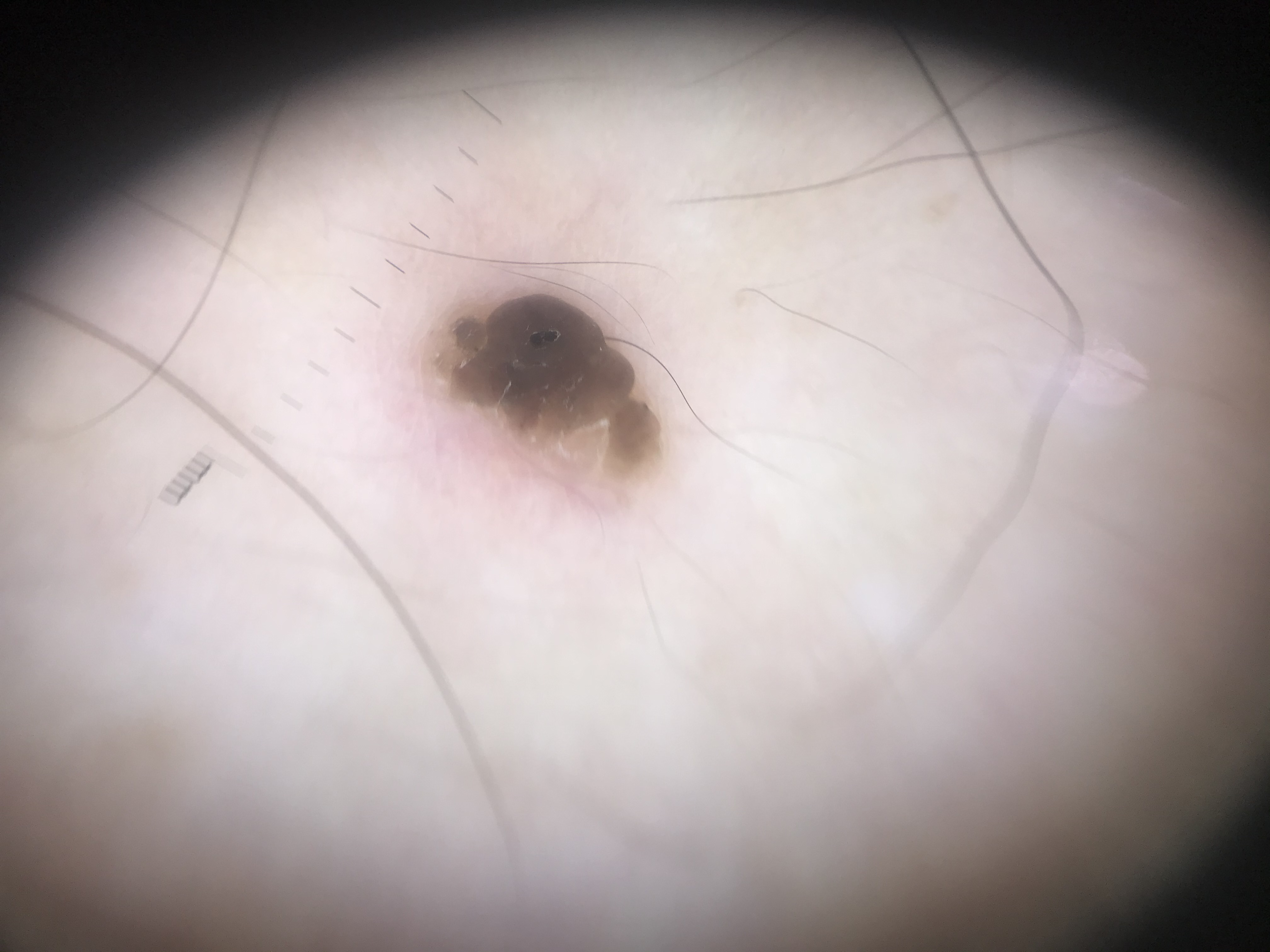Conclusion: Classified as a seborrheic keratosis.